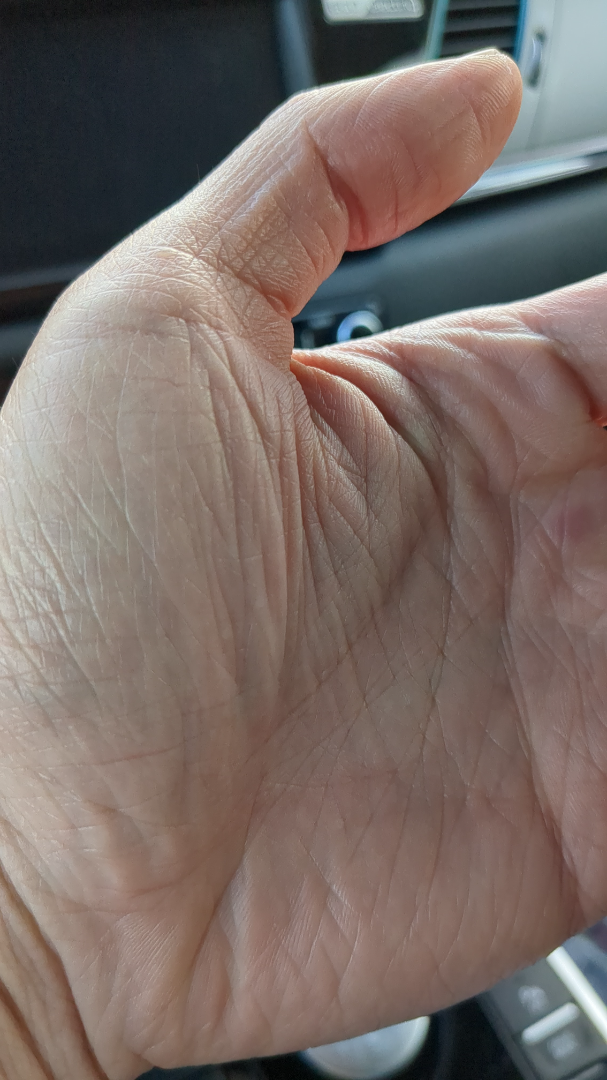<case>
<assessment>indeterminate</assessment>
</case>